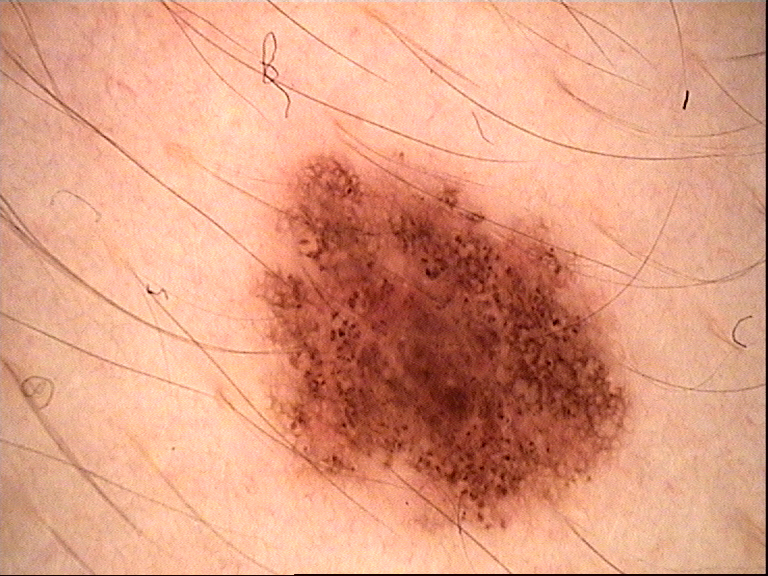{"diagnosis": {"name": "dysplastic compound nevus", "code": "cd", "malignancy": "benign", "super_class": "melanocytic", "confirmation": "expert consensus"}}